Dermoscopy of a skin lesion — 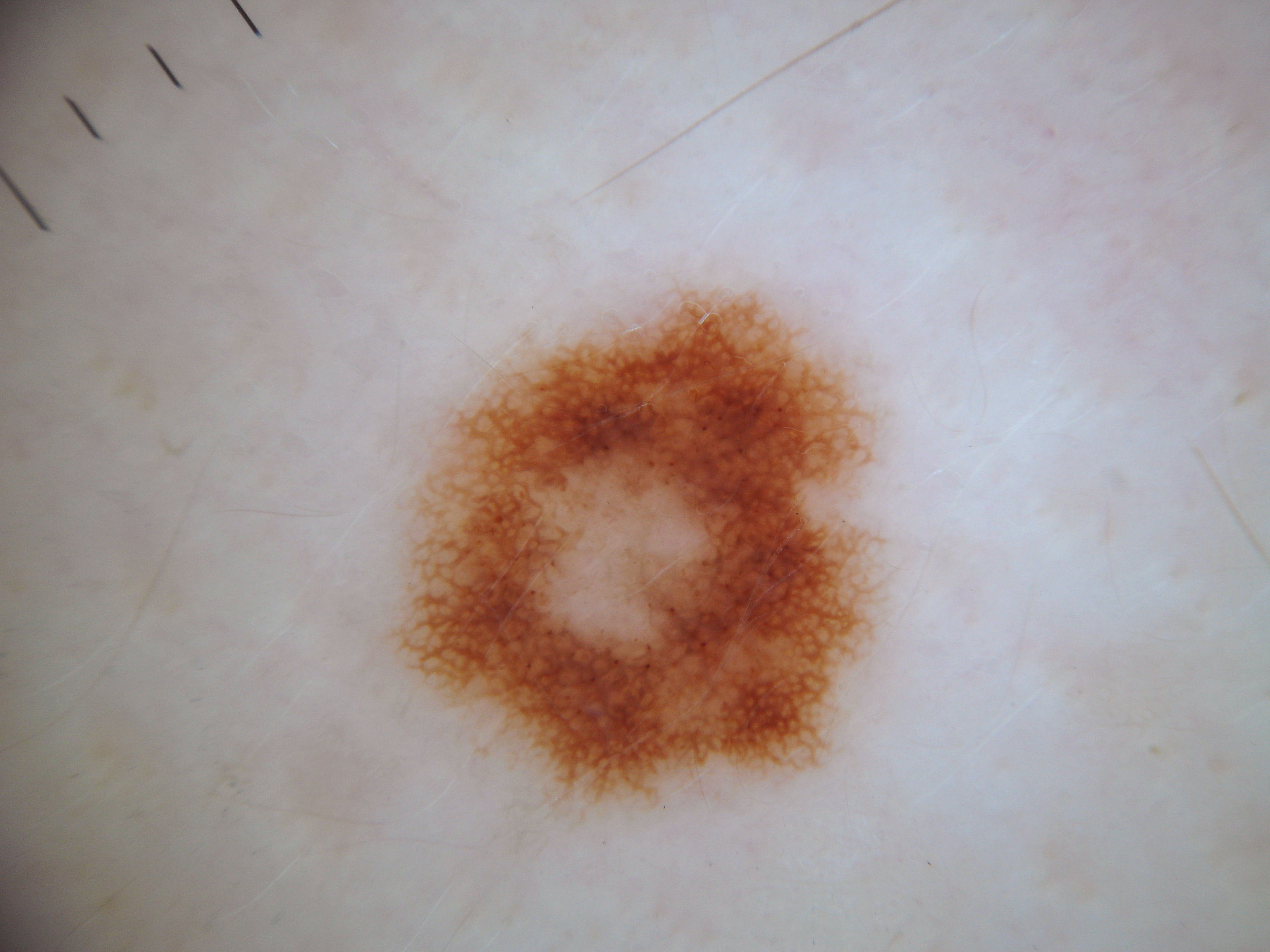On dermoscopy, the lesion shows pigment network. A moderately sized lesion. In (x1, y1, x2, y2) order, the lesion's extent is bbox=[370, 290, 884, 825]. Expert review diagnosed this as a melanocytic nevus, a benign lesion.